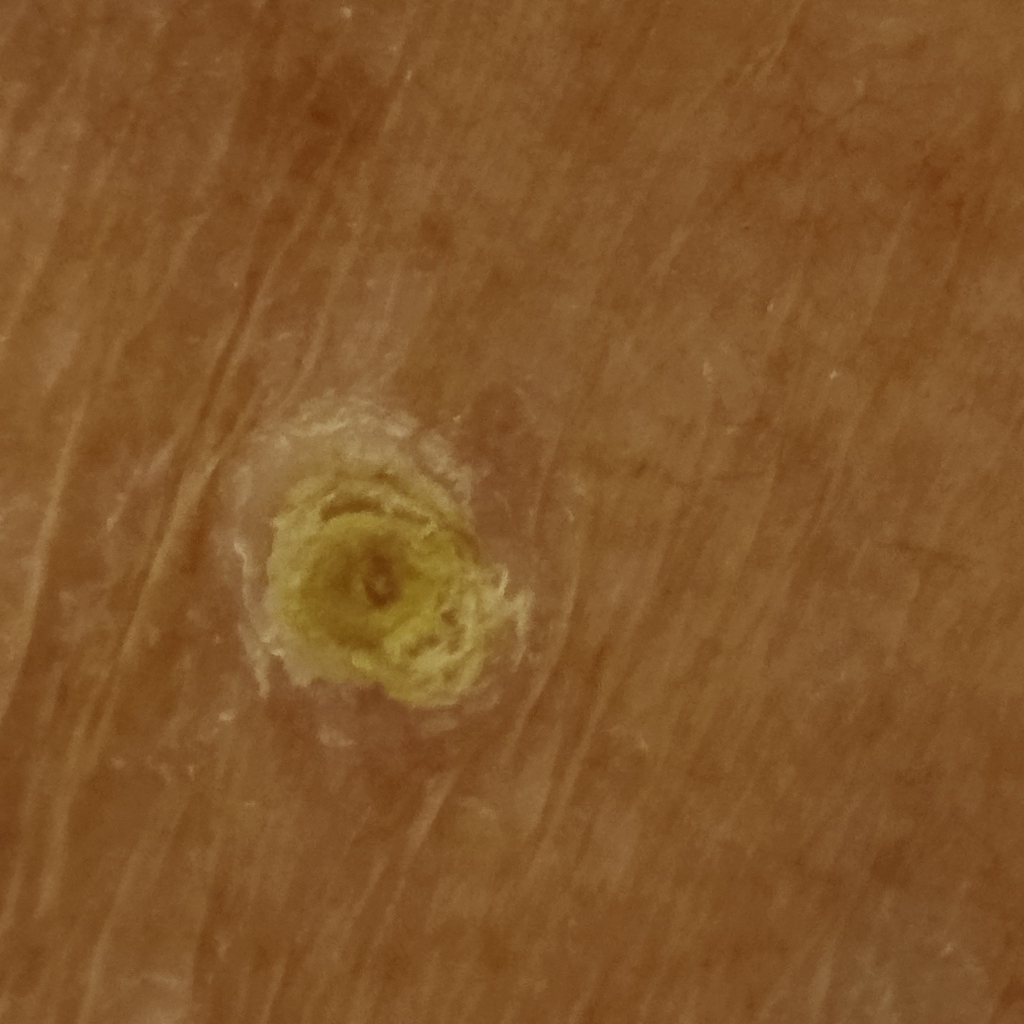Clinical context:
The patient says their skin tans without first burning. Imaged for a research study, with no referral diagnosis recorded. The lesion is on the torso. The lesion is about 12.5 mm across.
Impression:
The consensus diagnosis for this lesion was a squamous cell carcinoma.